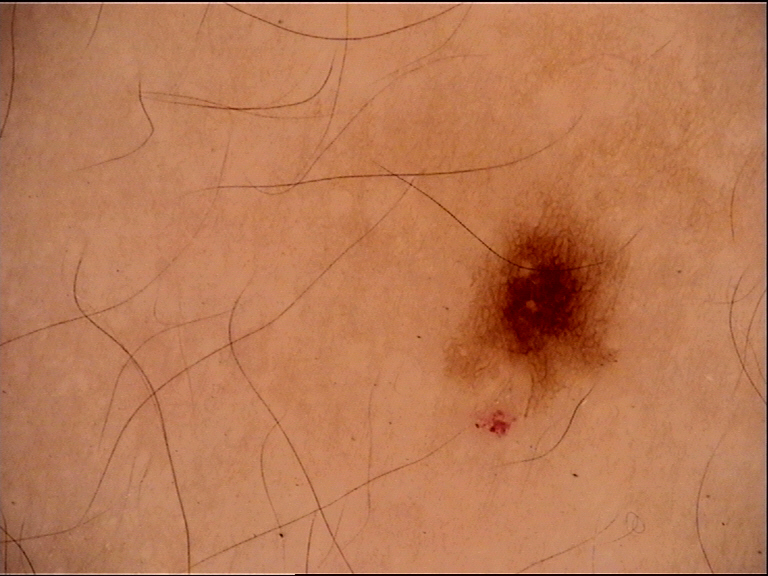A dermatoscopic image of a skin lesion. The architecture is that of a banal lesion. The diagnosis was a junctional nevus.